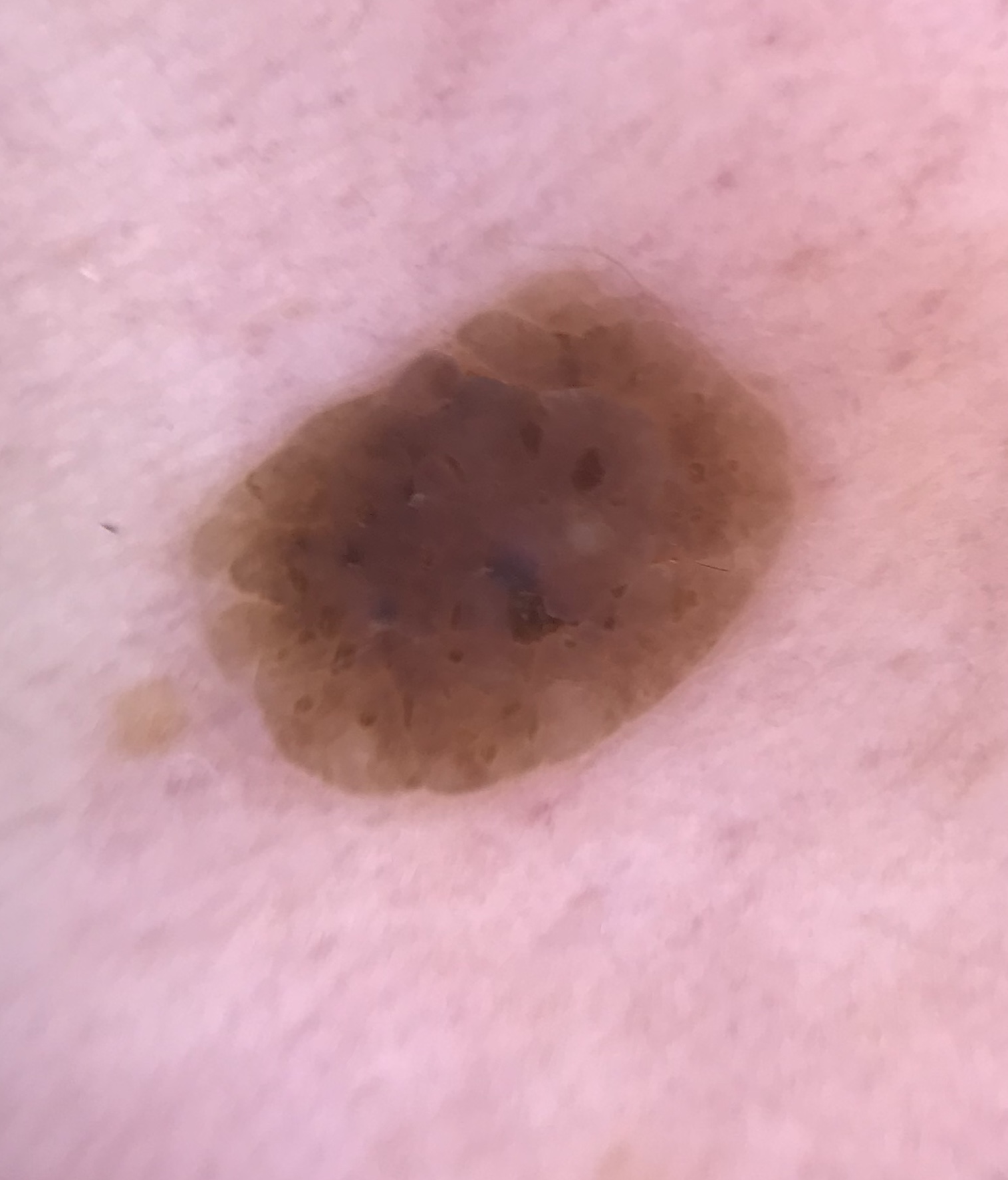Case:
• label — seborrheic keratosis (expert consensus)